A male patient roughly 60 years of age. Per the chart, a prior melanoma. A dermatoscopic image of a skin lesion.
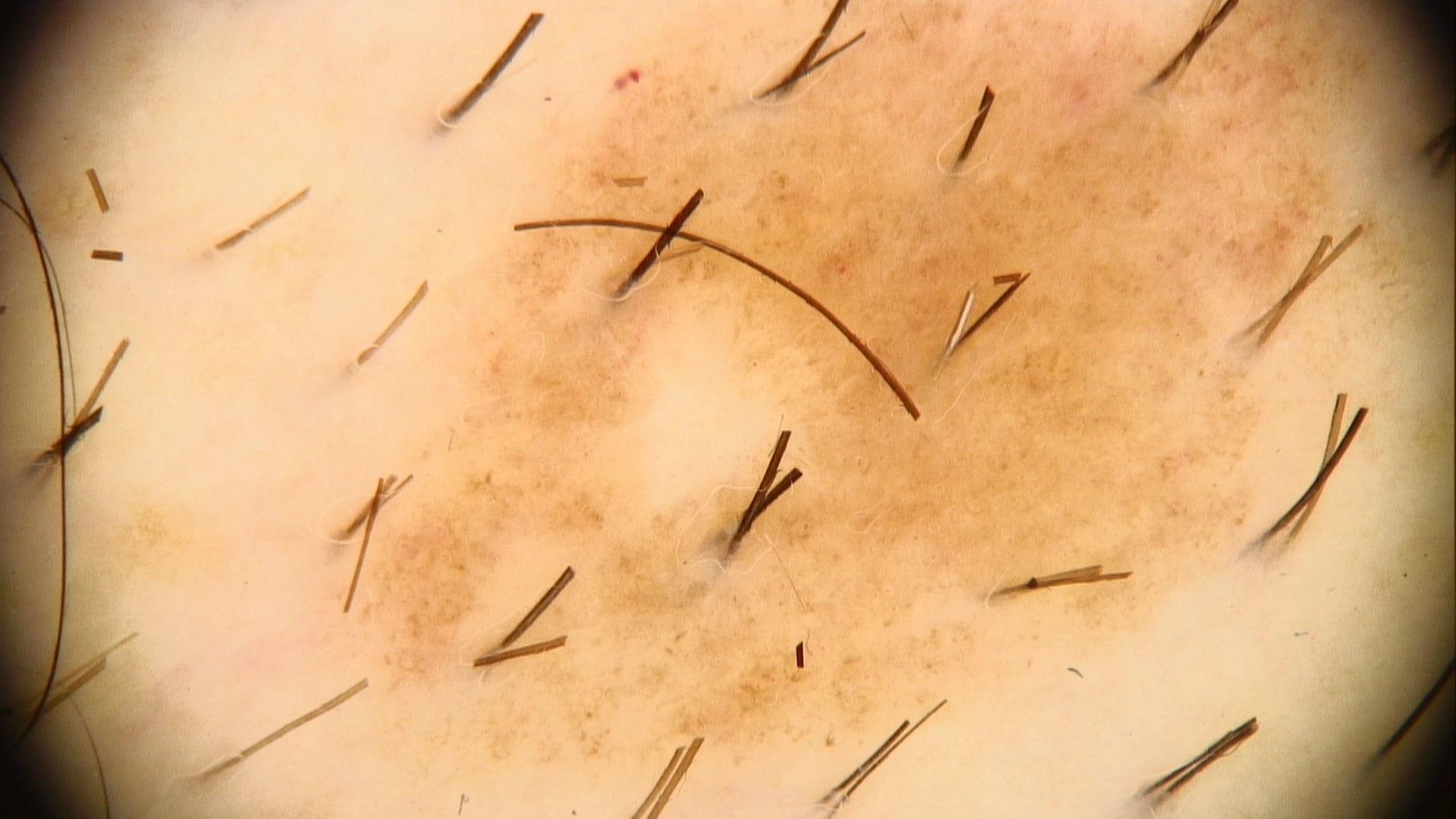Case:
– body site · the trunk
– diagnostic label · Nevus (clinical impression)